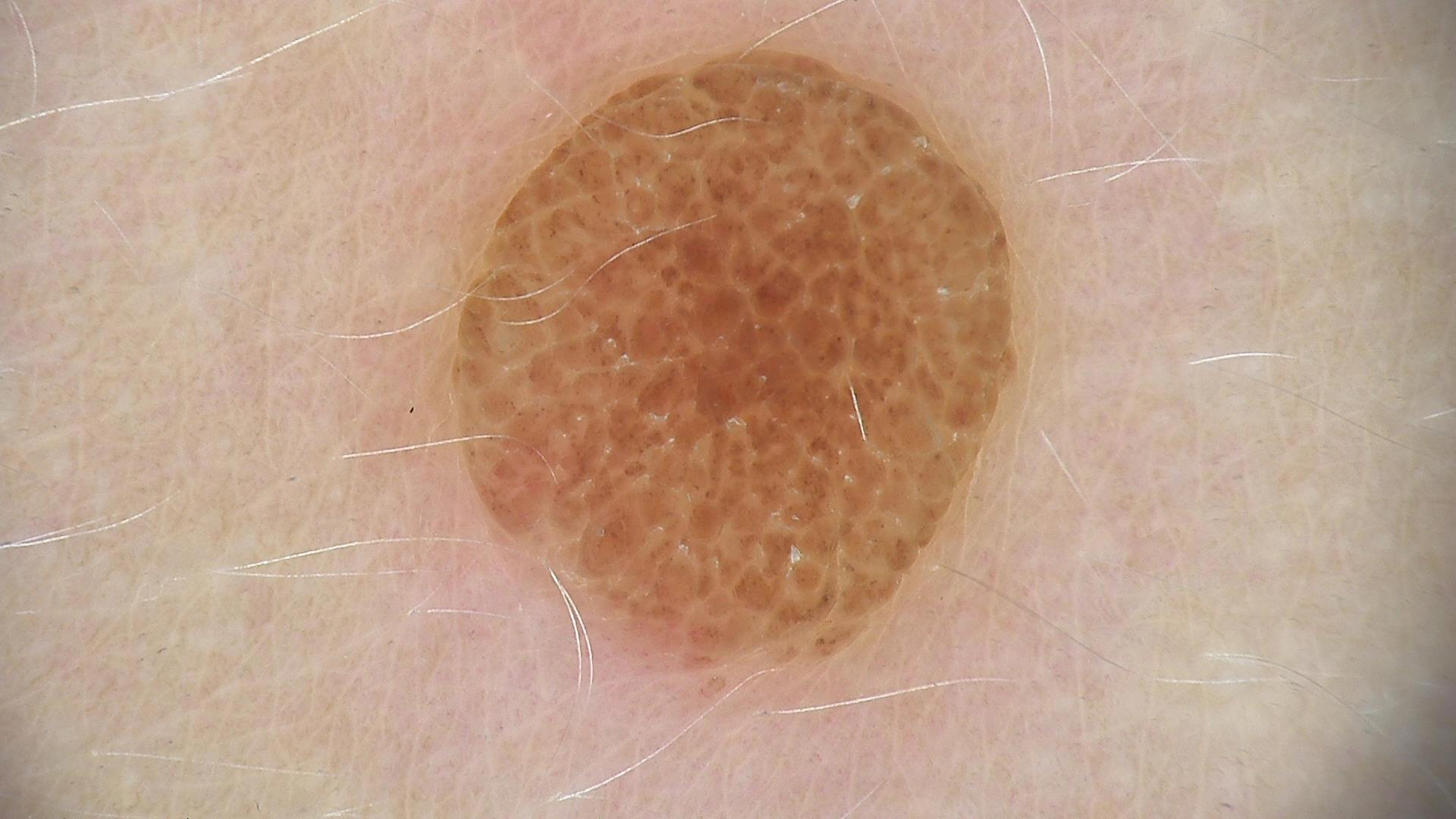A dermoscopy image of a single skin lesion. The diagnosis was a banal lesion — a compound nevus.